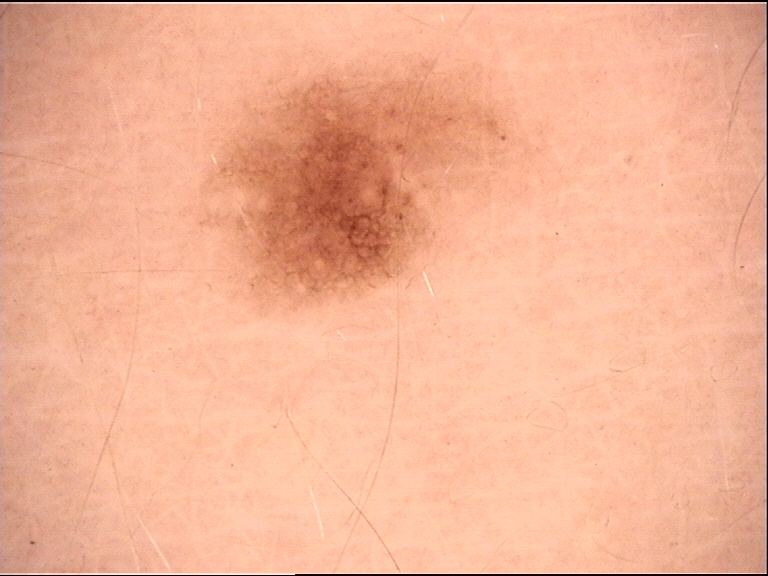Findings: Dermoscopy of a skin lesion. Conclusion: Labeled as a benign lesion — a dysplastic junctional nevus.